The subject is 30–39, female · the photograph was taken at an angle · located on the top or side of the foot.
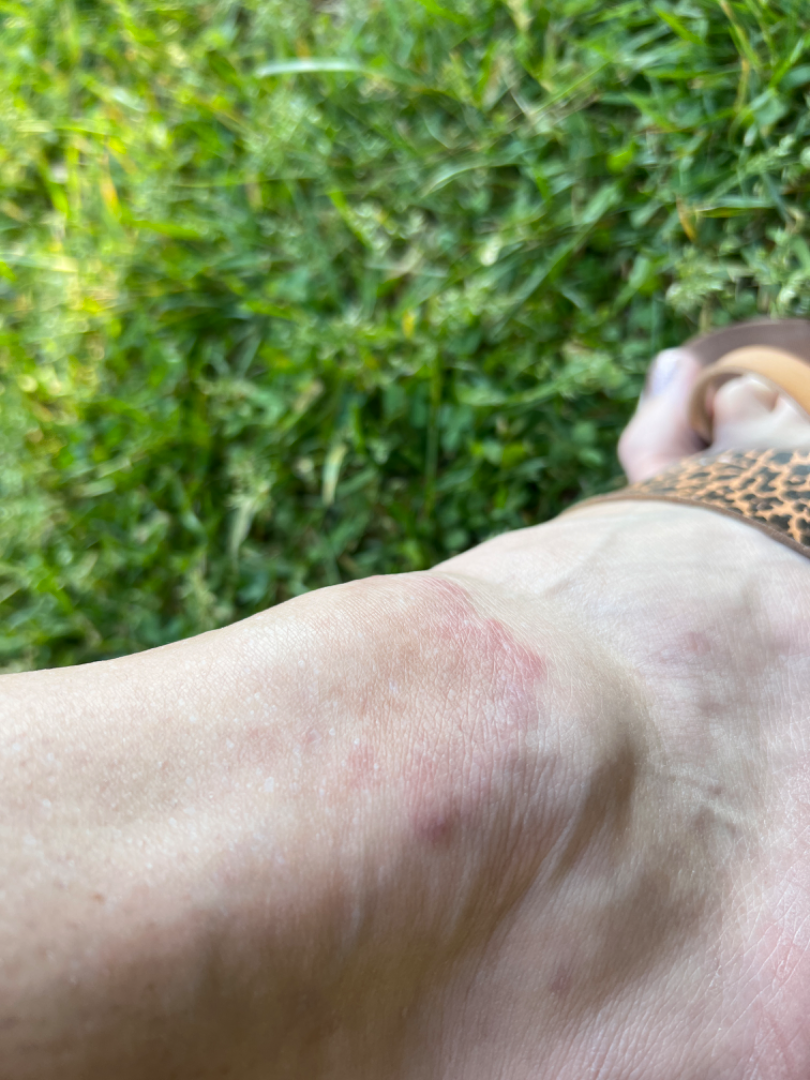The condition has been present for more than one year.
Texture is reported as flat.
The patient indicates enlargement.
On remote dermatologist review, Granuloma annulare (leading).